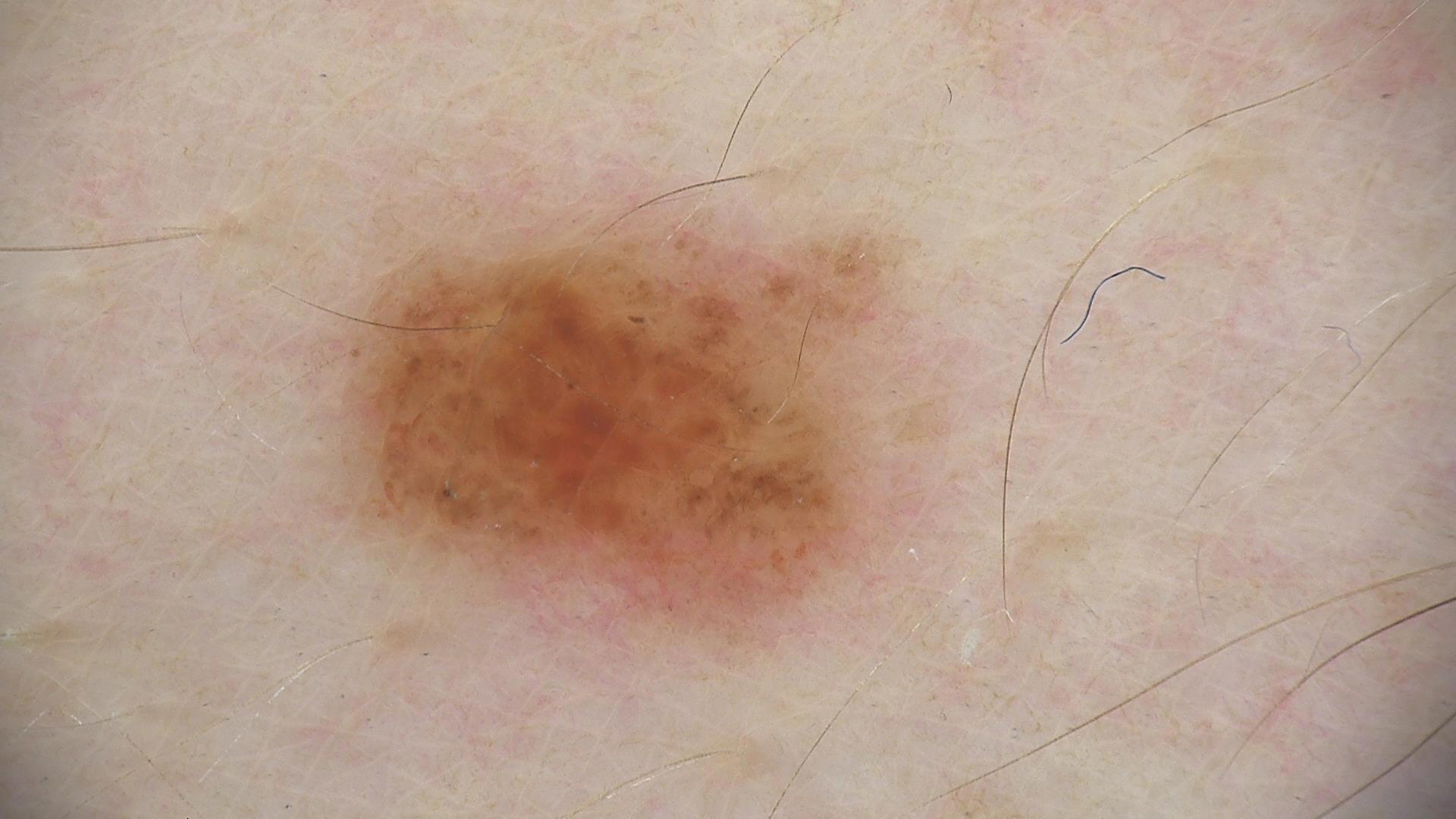| field | value |
|---|---|
| imaging | dermatoscopy |
| class | compound nevus (expert consensus) |